The patient is 18–29, male · reported duration is about one day · the patient considered this skin that appeared healthy to them · the contributor notes the lesion is flat · this image was taken at an angle.
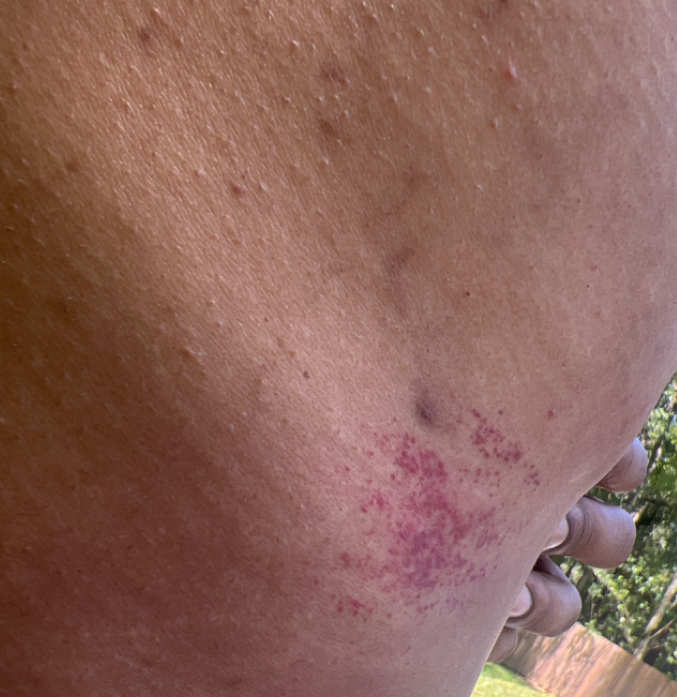Findings:
• impression — the differential includes Leukocytoclastic Vasculitis and Purpura, with no clear leading consideration